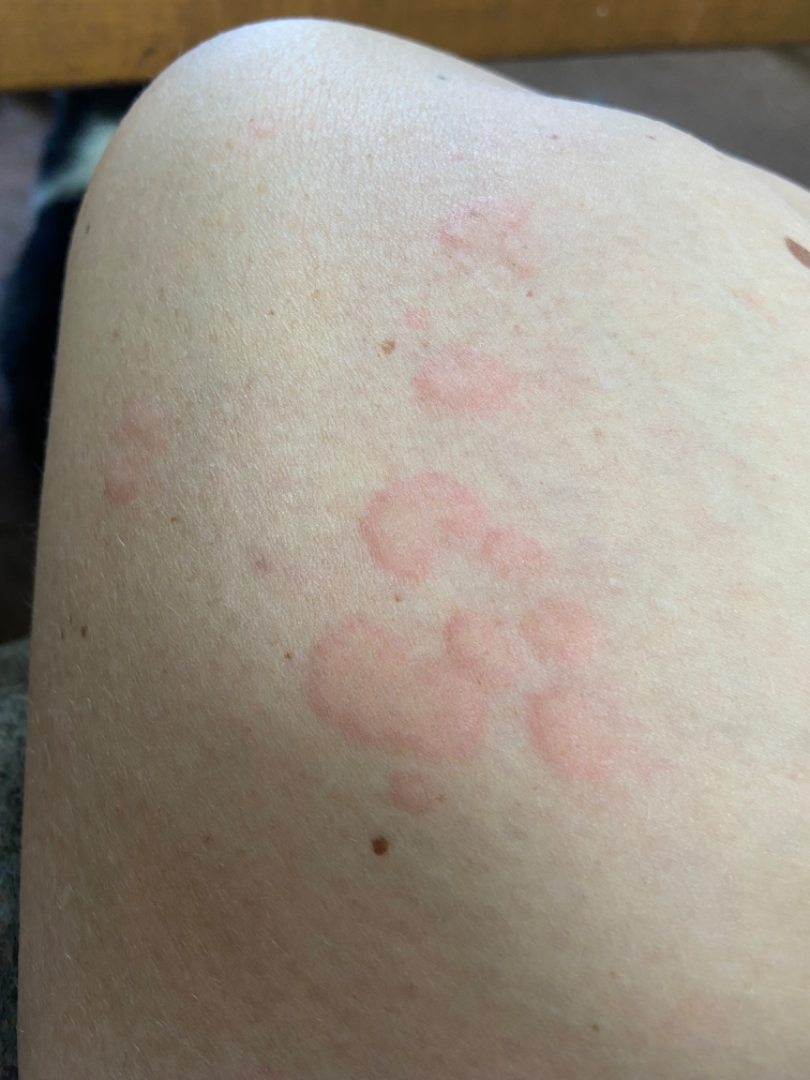constitutional symptoms=fatigue
photo taken=close-up
body site=arm, head or neck, leg and front of the torso
patient's own categorization=a rash
patient-reported symptoms=bothersome appearance, itching and enlargement
present for=less than one week
differential diagnosis=the impression on review was Urticaria